Non-clinician graders estimated Monk Skin Tone 3 or 5 · this image was taken at an angle — 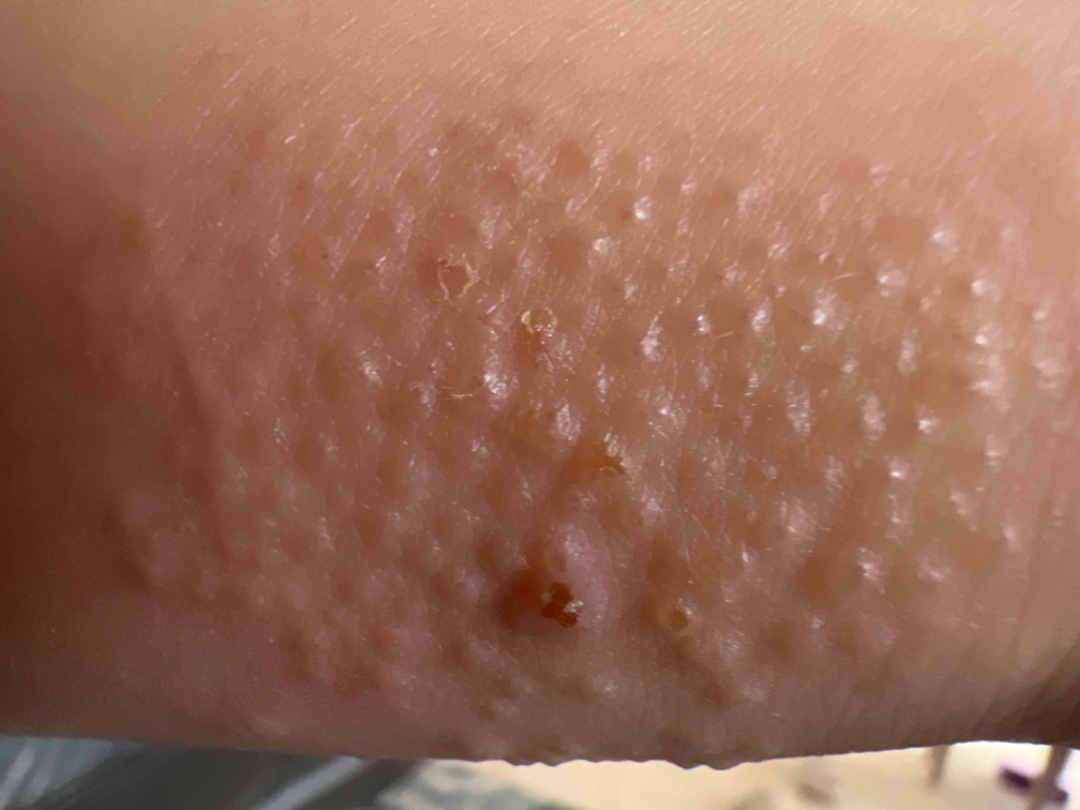assessment: indeterminate from the photograph